A dermoscopic image of a skin lesion. A female patient, aged 48-52:
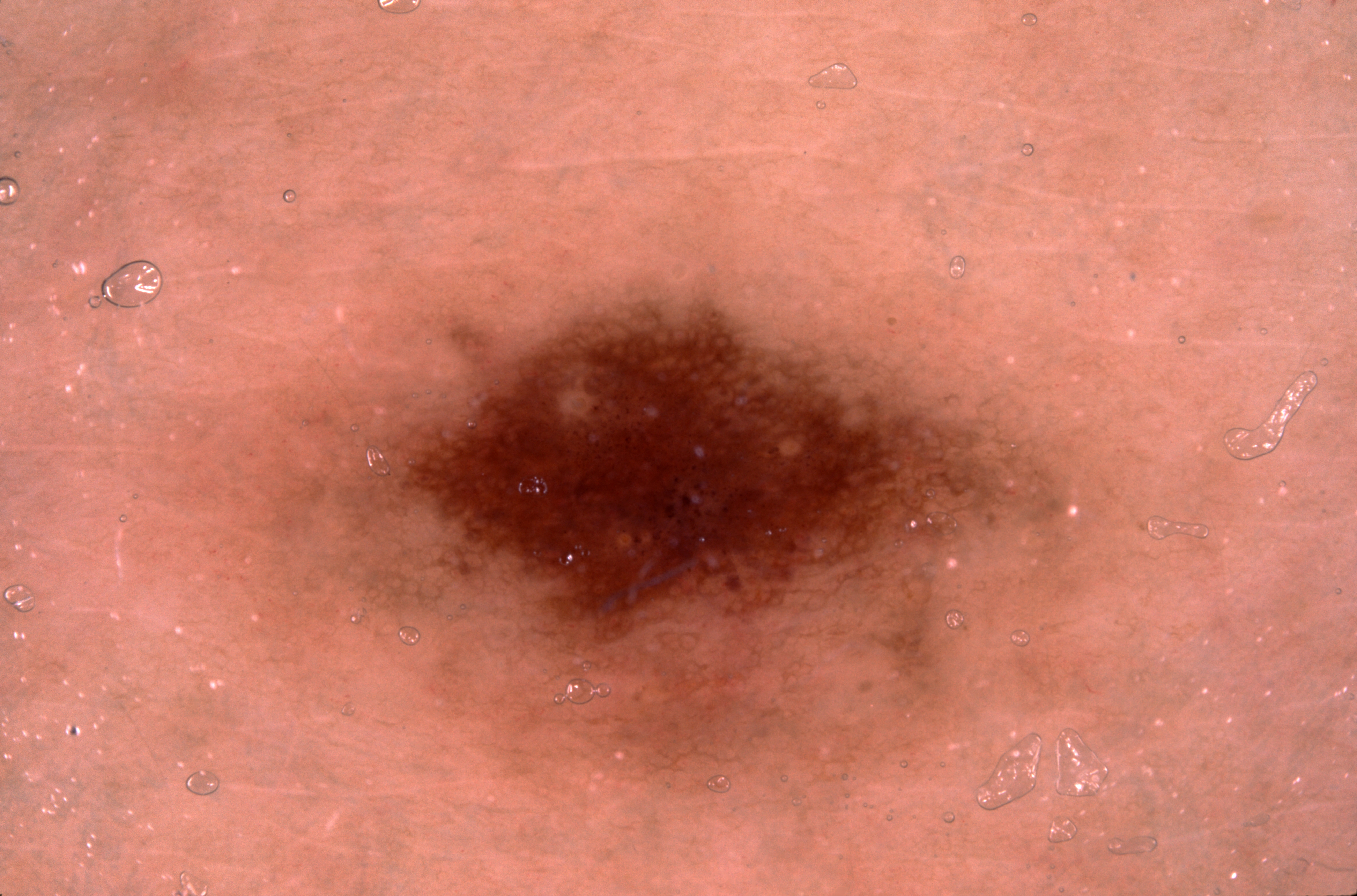<record>
<lesion_extent>large</lesion_extent>
<dermoscopic_features>
  <present>pigment network</present>
  <absent>milia-like cysts, negative network, streaks</absent>
</dermoscopic_features>
<lesion_location>
  <bbox_xyxy>136, 210, 1211, 867</bbox_xyxy>
</lesion_location>
<diagnosis>
  <name>melanocytic nevus</name>
  <malignancy>benign</malignancy>
  <lineage>melanocytic</lineage>
  <provenance>clinical</provenance>
</diagnosis>
</record>